A skin lesion imaged with a dermatoscope: 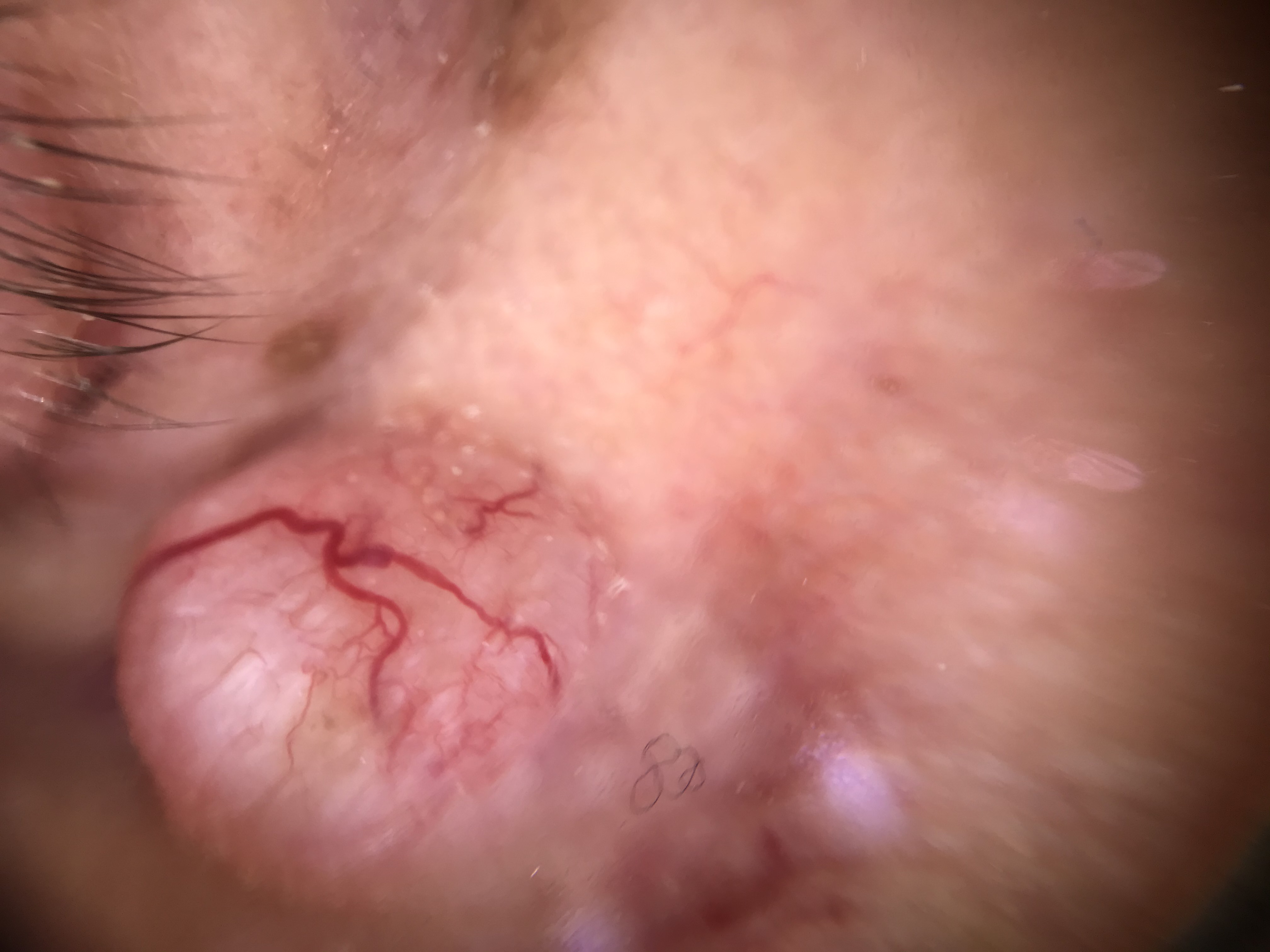Histopathologically confirmed as a keratinocytic, malignant lesion — a basal cell carcinoma.